Located on the arm, head or neck and leg; reported duration is less than one week; male subject, age 30–39; the photo was captured at a distance:
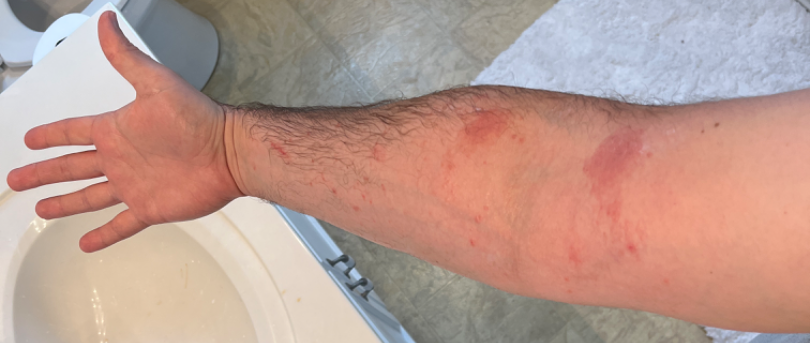The case was indeterminate on photographic review.